The contributor notes bothersome appearance · present for about one day · the affected area is the leg · this image was taken at an angle · the lesion is described as fluid-filled and raised or bumpy · no relevant systemic symptoms:
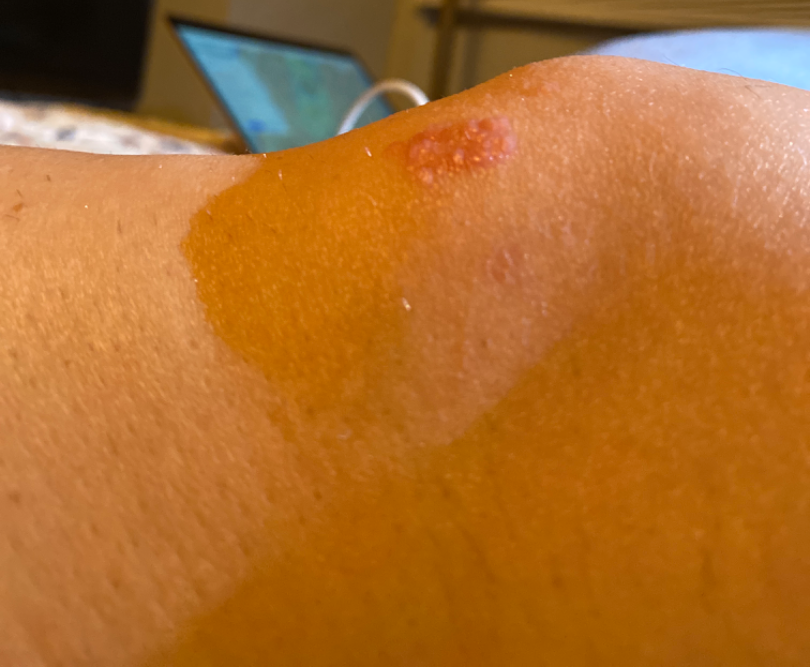{
  "assessment": "indeterminate"
}